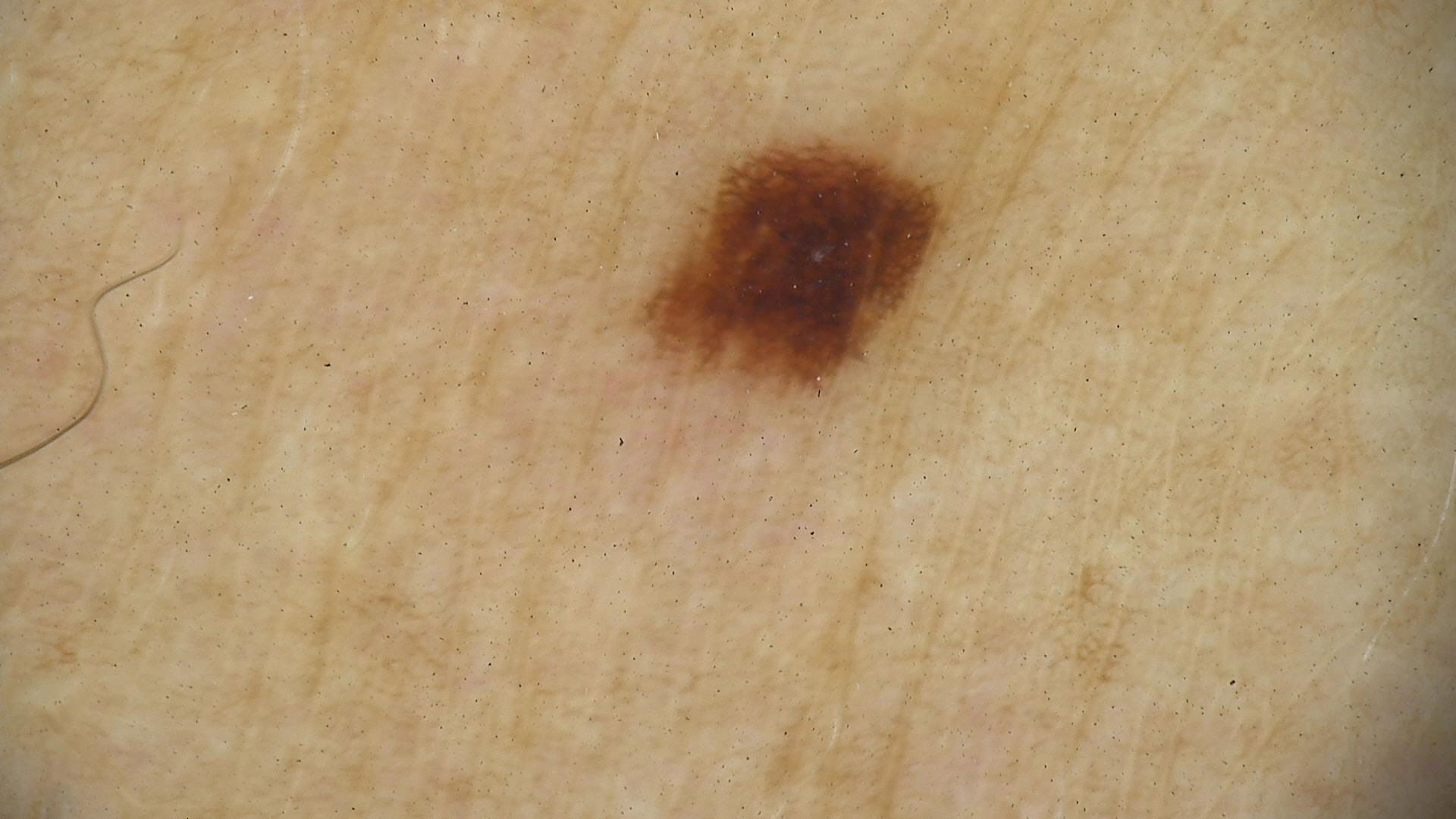  image: dermatoscopy
  diagnosis:
    name: dysplastic junctional nevus
    code: jd
    malignancy: benign
    super_class: melanocytic
    confirmation: expert consensus